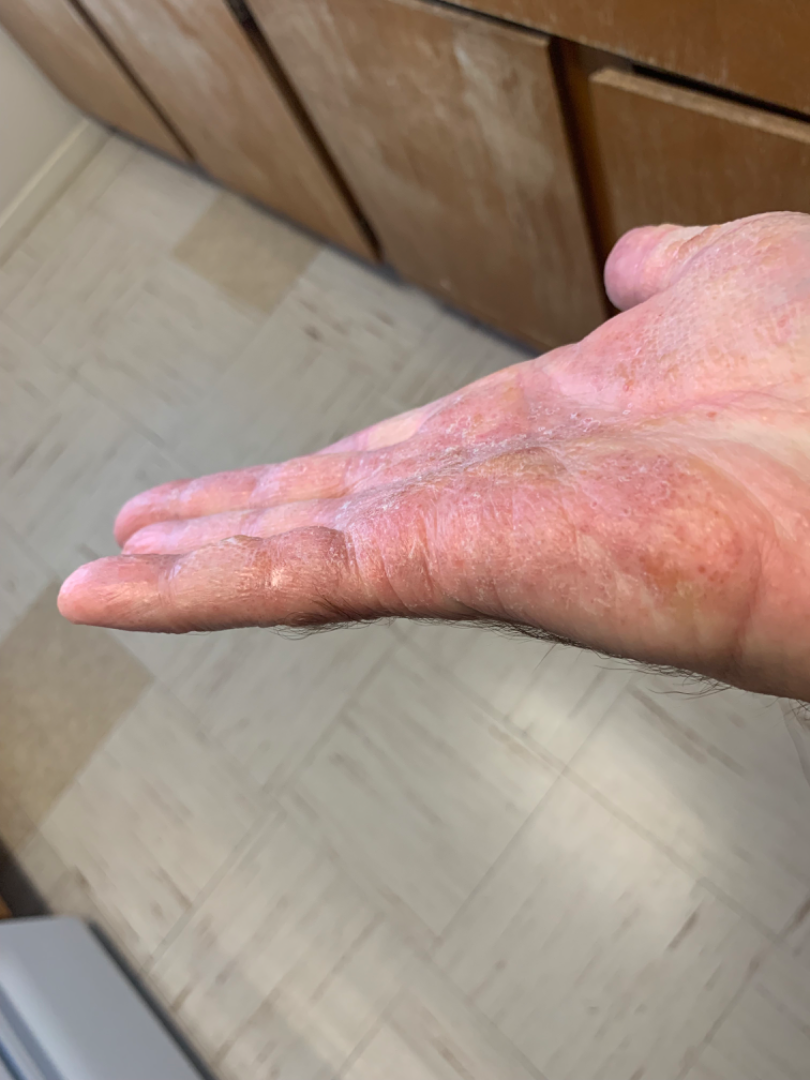{
  "shot_type": "at an angle",
  "differential": {
    "leading": [
      "Eczema"
    ],
    "considered": [
      "Irritant Contact Dermatitis"
    ]
  }
}